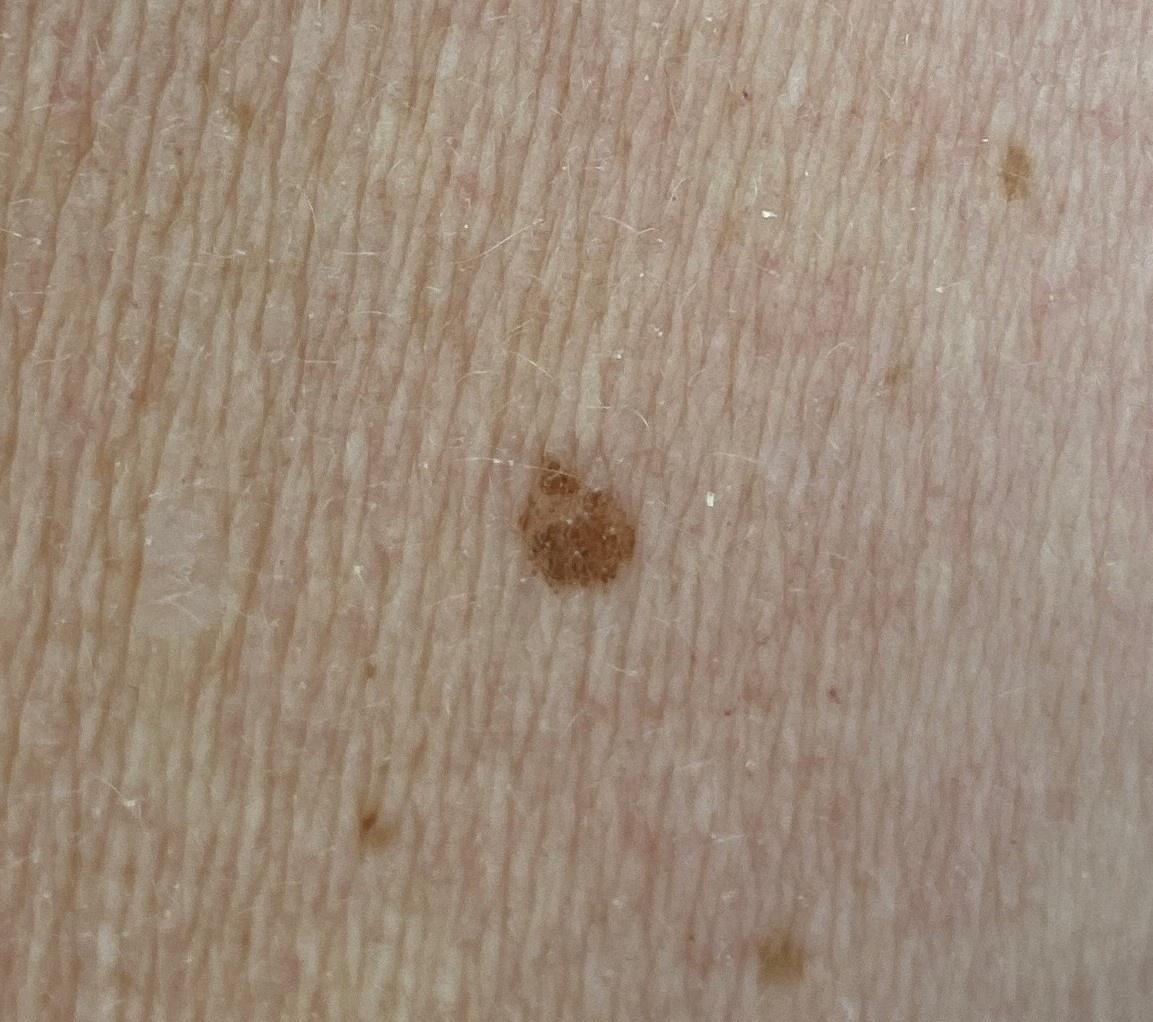melanoma_history:
  personal_hx_melanoma: true
patient:
  age_approx: 60
  sex: female
skin_type: II
lesion_location:
  region: an upper extremity
diagnosis:
  name: Nevus
  malignancy: benign
  confirmation: expert clinical impression
  lineage: melanocytic